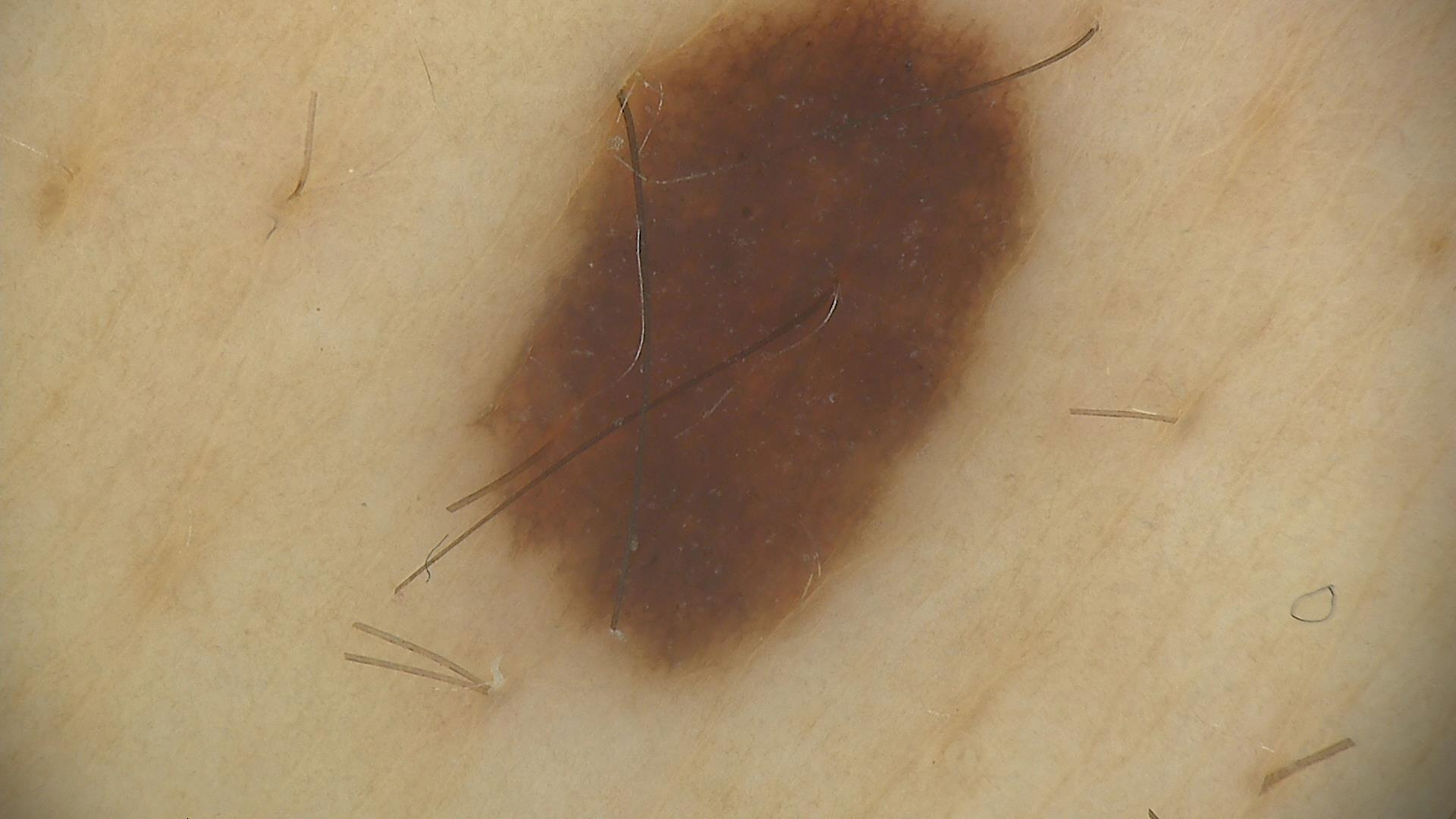The diagnosis was a dysplastic junctional nevus.